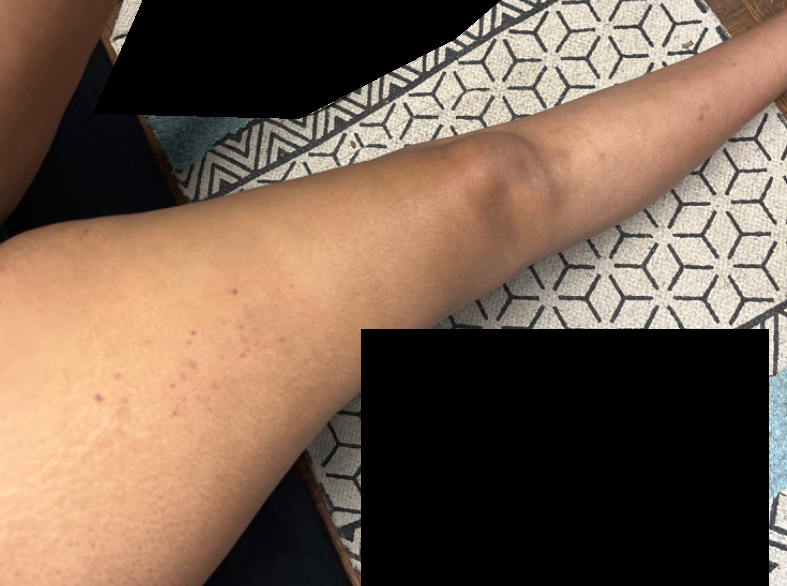assessment=unable to determine
framing=at a distance
anatomic site=leg